The contributor is a female aged 18–29. The photograph was taken at an angle — 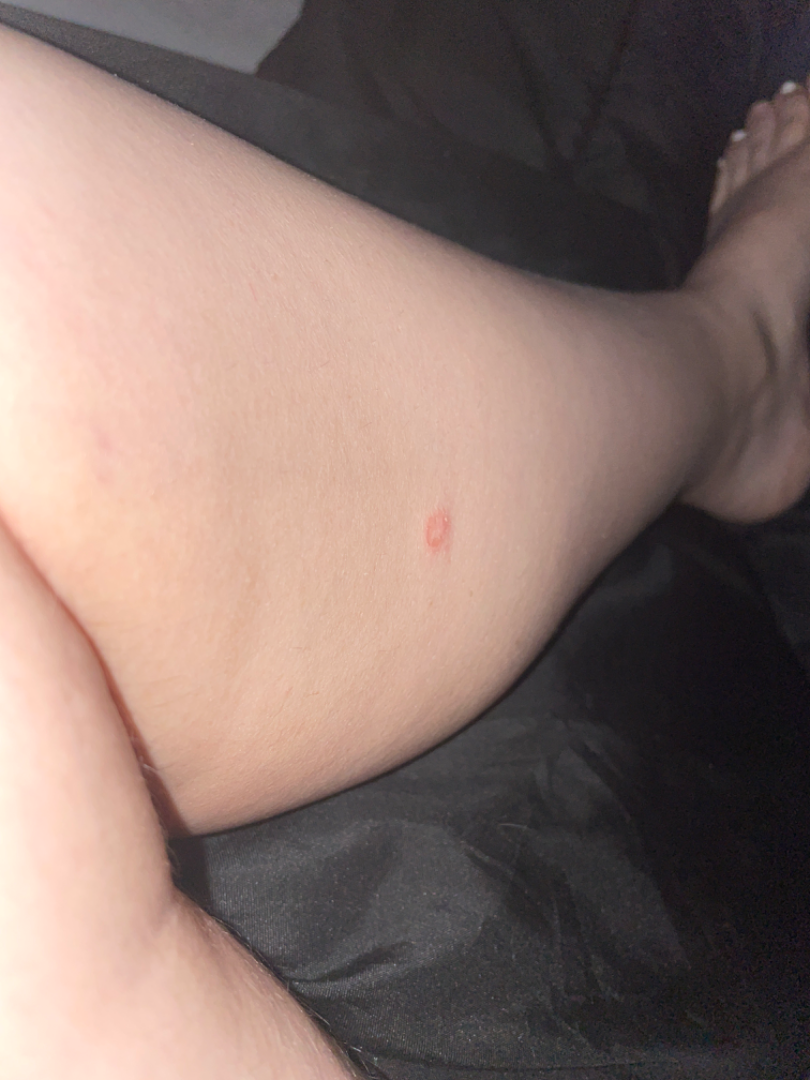{"assessment": "indeterminate from the photograph"}